The photo was captured at a distance — 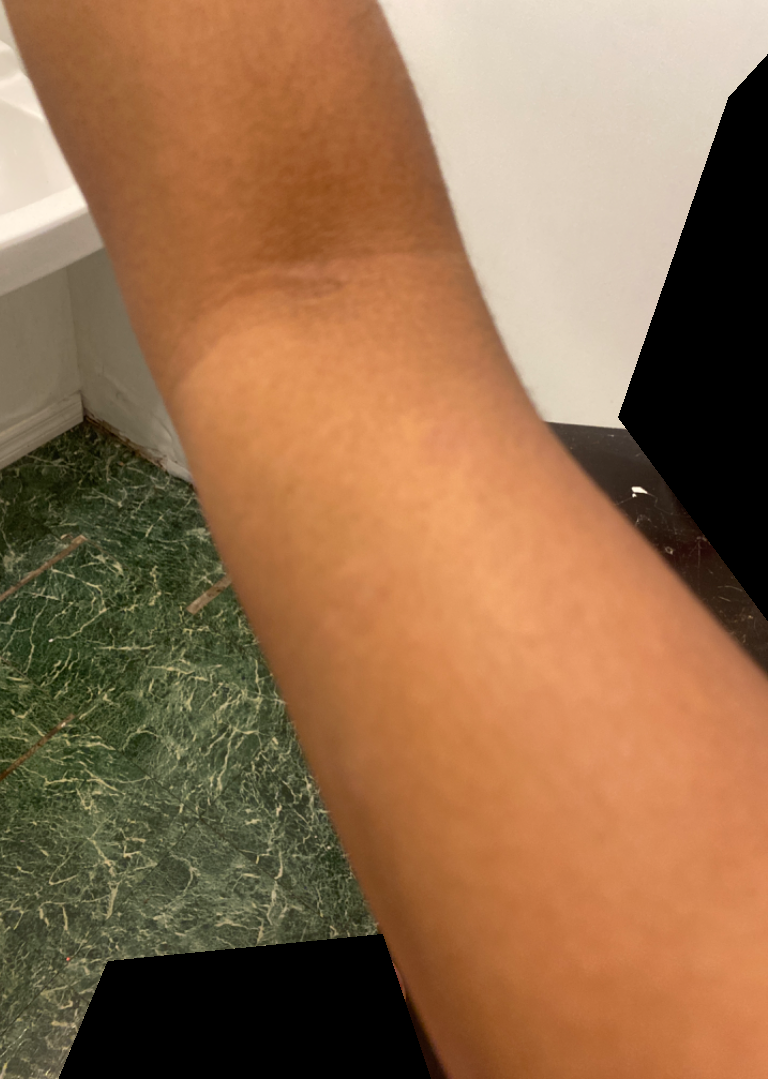No clear dermatological pathology was apparent in the photograph.